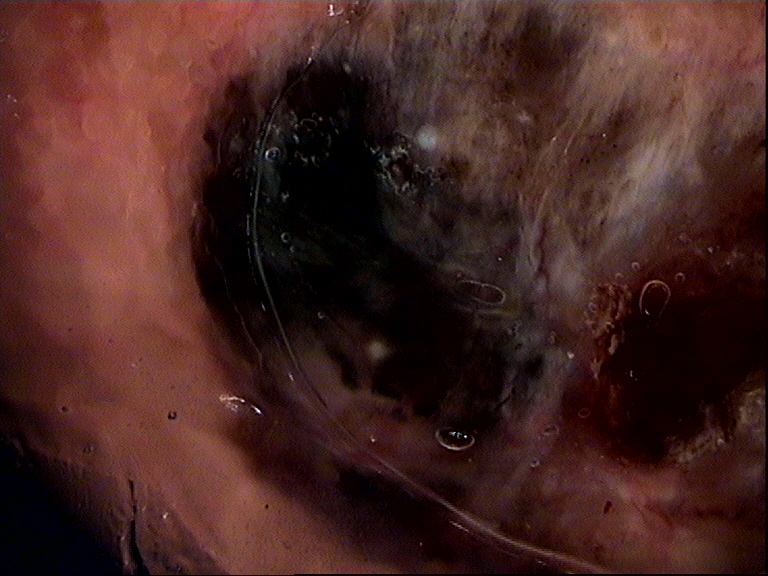image type = dermoscopy
diagnostic label = basal cell carcinoma (biopsy-proven)